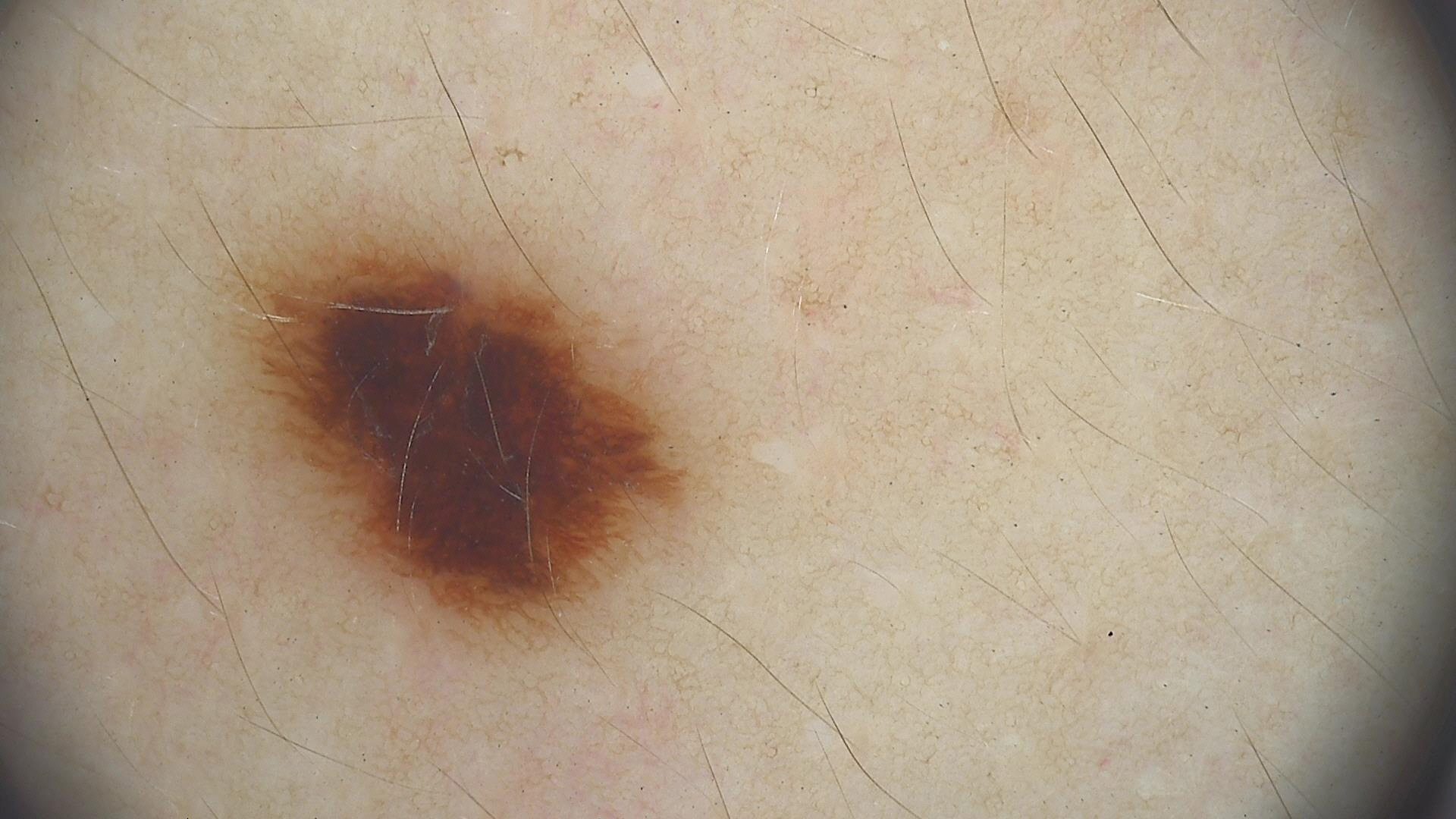The diagnosis was a dysplastic junctional nevus.